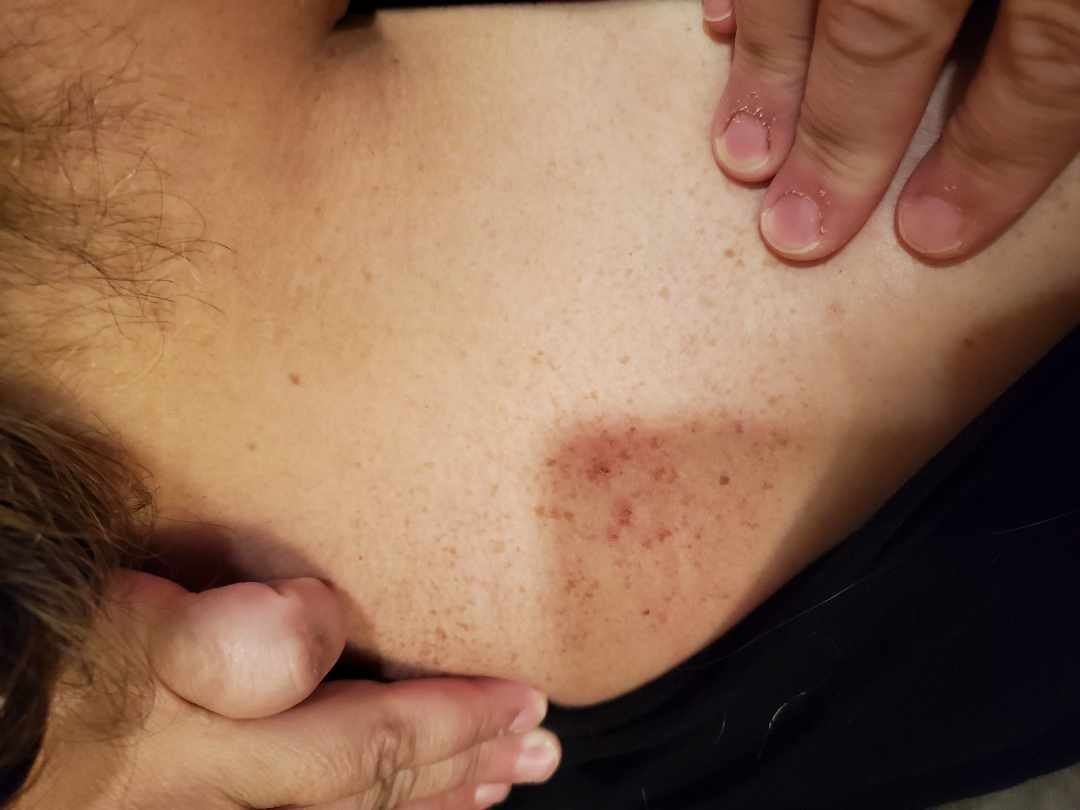assessment: could not be assessed; photo taken: close-up.